The arm and back of the hand are involved; self-categorized by the patient as a rash; the patient indicates the condition has been present for one to three months; this image was taken at an angle; the patient reported no relevant symptoms from the lesion; the lesion is described as raised or bumpy — 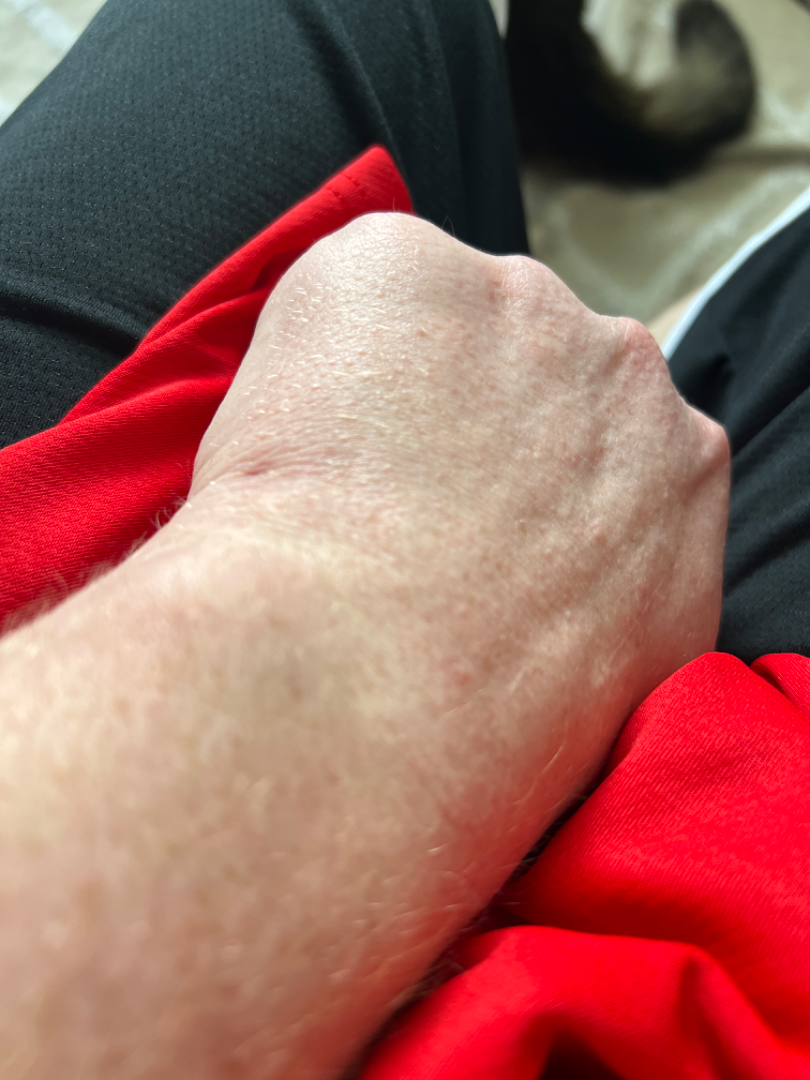assessment=not assessable.